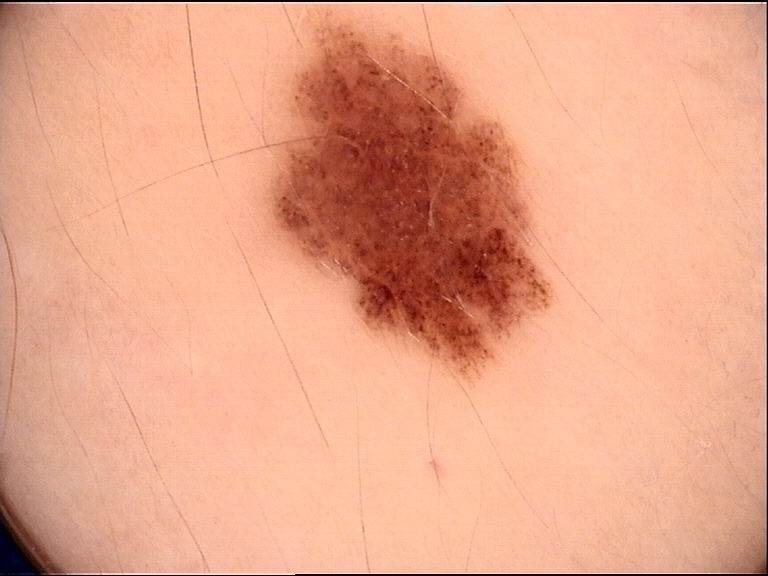The diagnosis was a dysplastic junctional nevus.